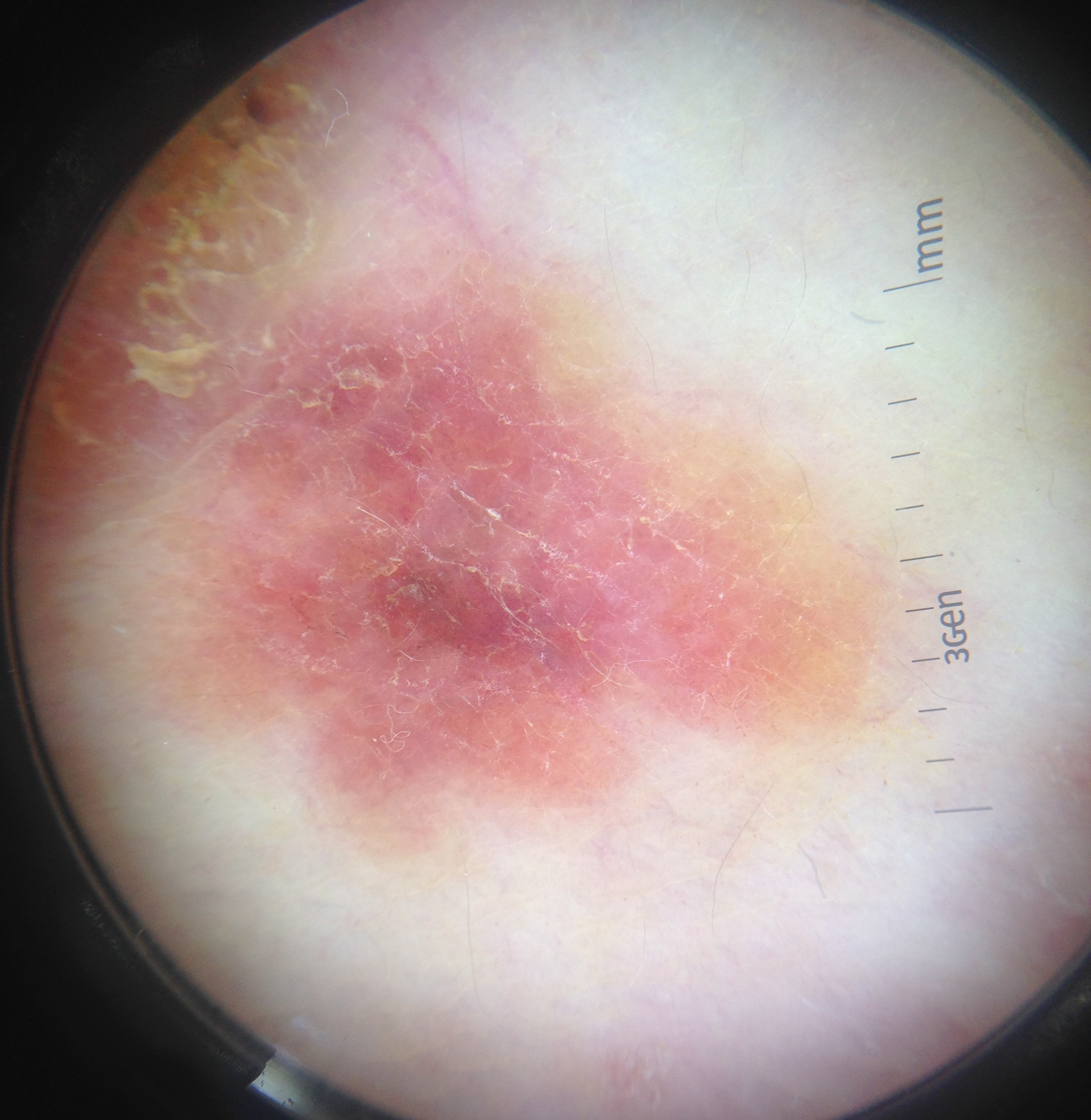image type: dermoscopy, diagnosis: Bowen's disease (biopsy-proven).